A dermoscopic image of a skin lesion.
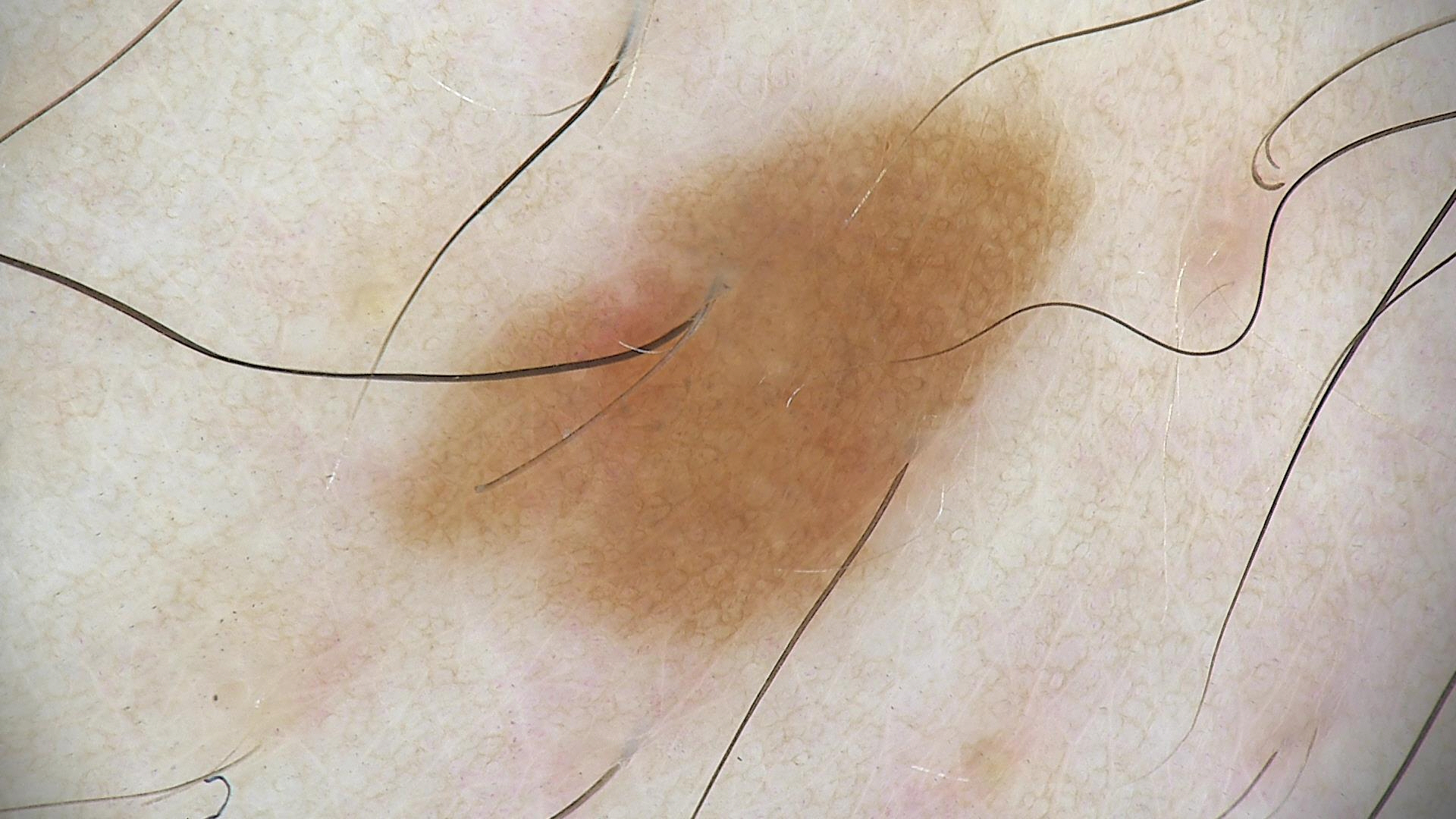* diagnostic label — dysplastic junctional nevus (expert consensus)